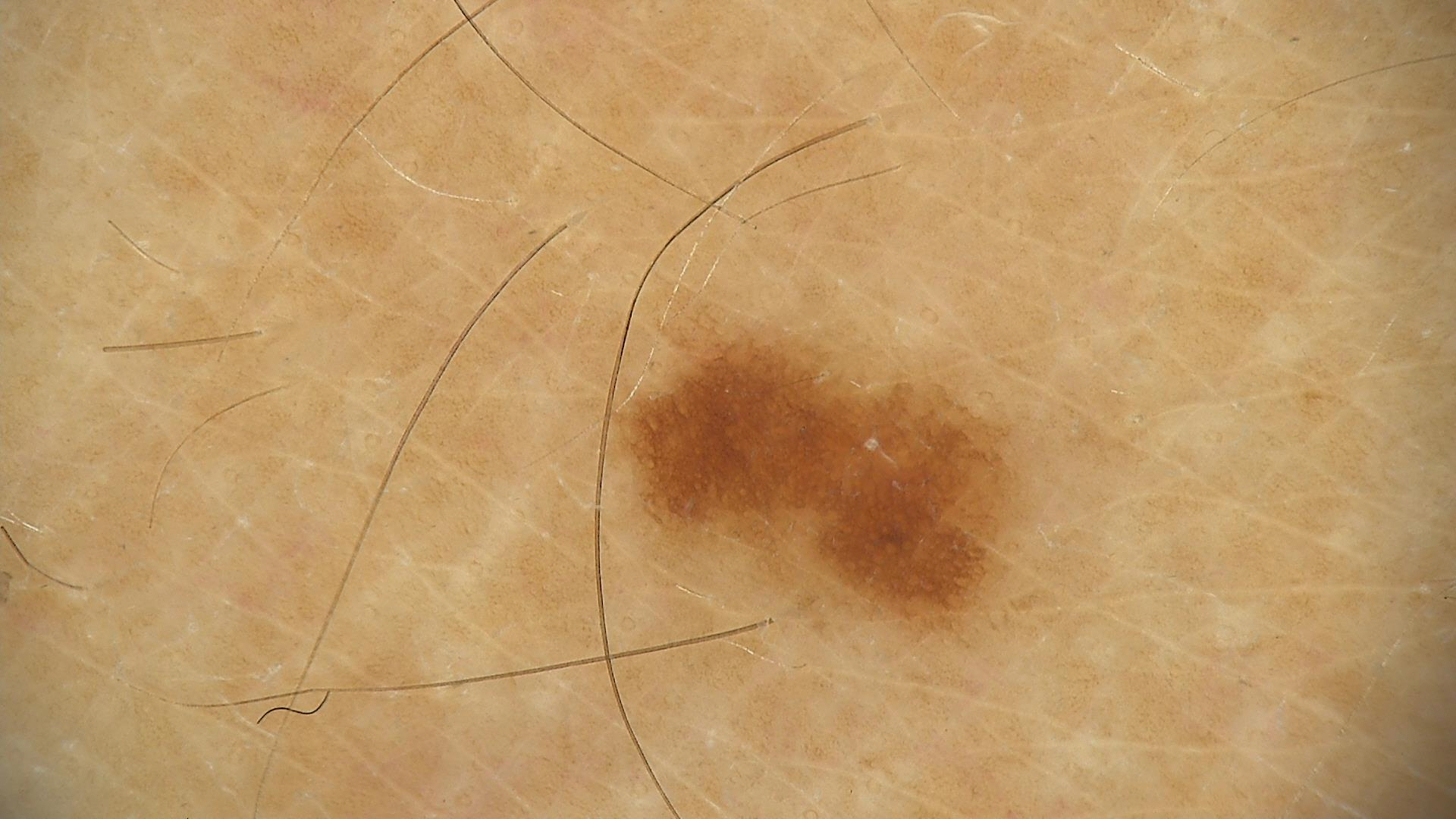Findings: A dermoscopy image of a single skin lesion. Conclusion: Consistent with a dysplastic junctional nevus.